Dermoscopy of a skin lesion.
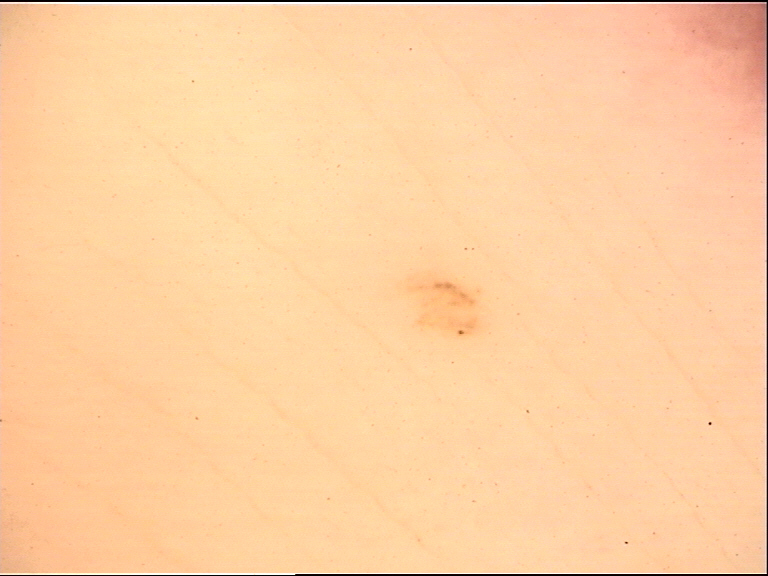Diagnosed as an acral dysplastic junctional nevus.